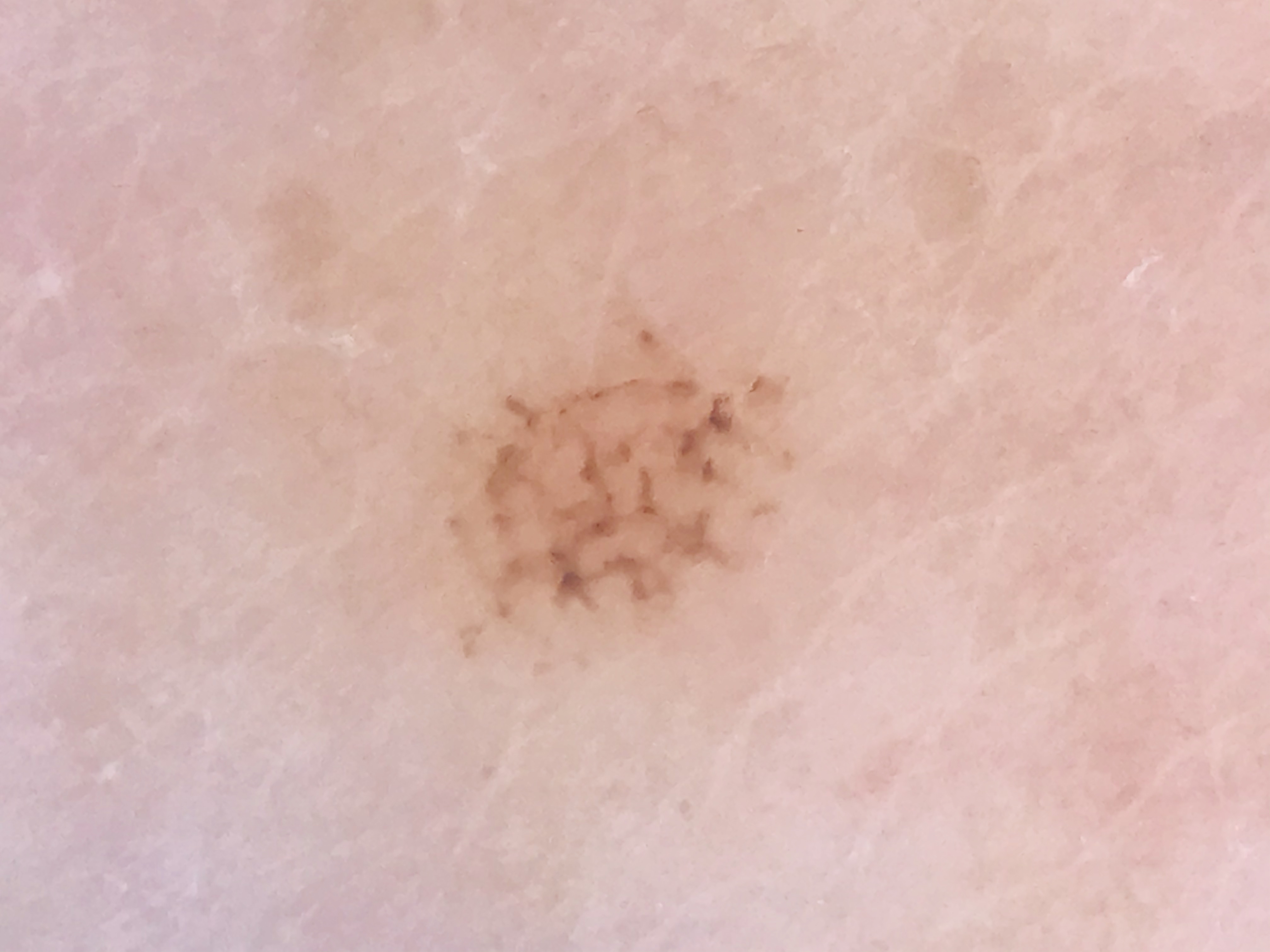Conclusion:
The diagnostic label was an acral dysplastic junctional nevus.